The patient describes having few moles overall. The patient says their skin tans without first burning. A dermatoscopic image of a skin lesion. On a questionnaire the patient reported a personal history of skin cancer and a personal history of cancer. The referring clinician suspected basal cell carcinoma. A female subject 60 years old — 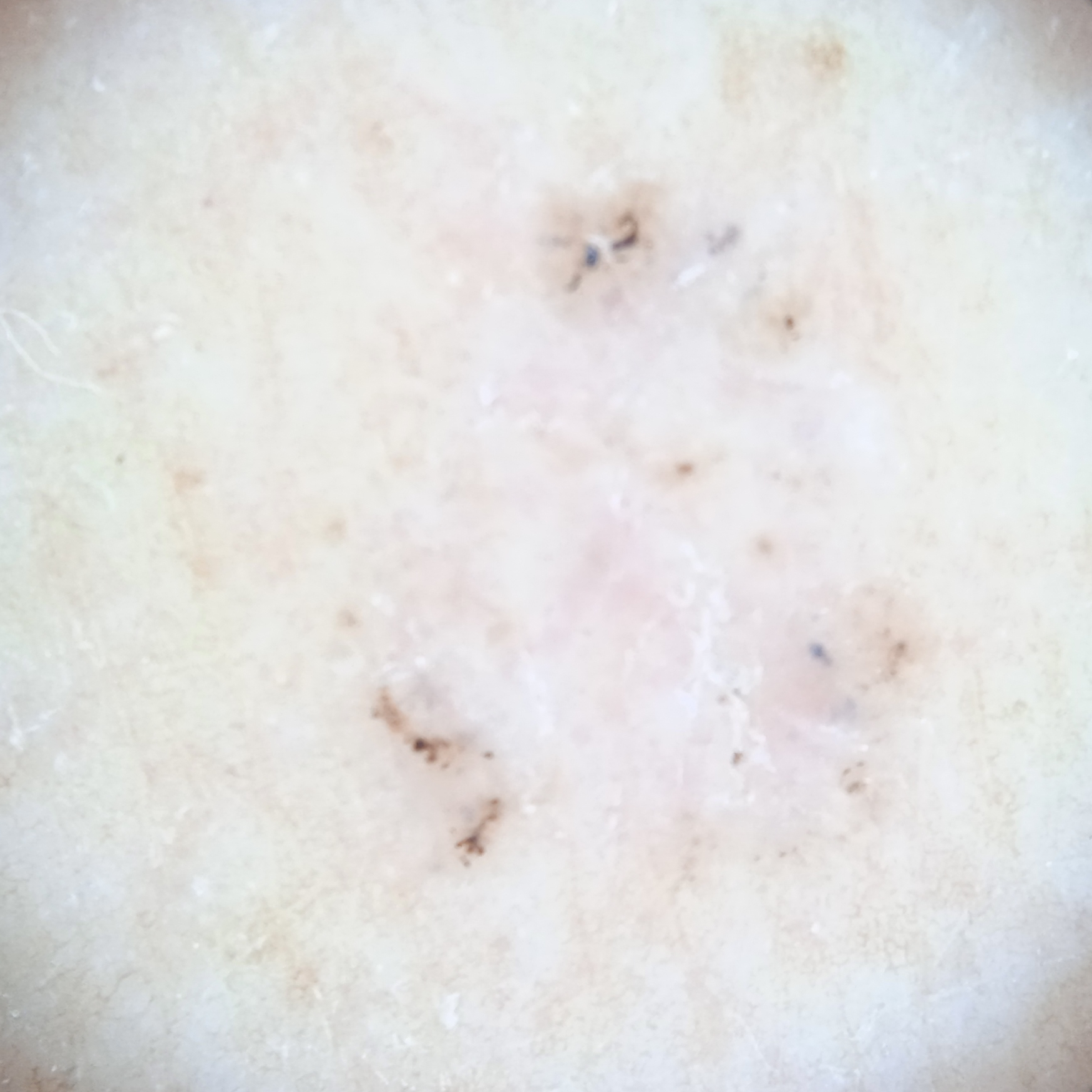Case:
• anatomic site · the back
• size · 7.8 mm
• diagnostic label · basal cell carcinoma (dermatologist consensus)